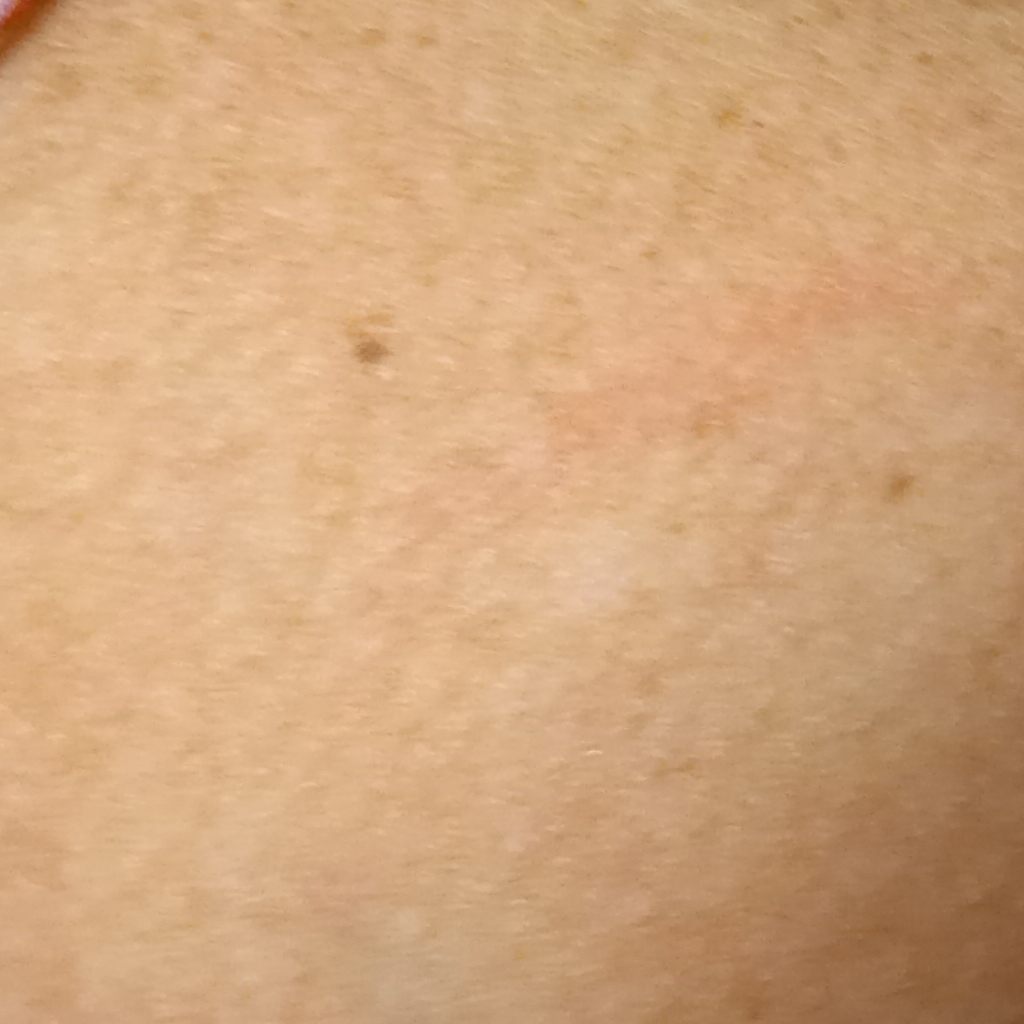The patient says their skin reddens with sun exposure.
By self-report, a personal history of skin cancer, no personal history of cancer, and no immunosuppression.
A female patient age 67.
Acquired for a research image collection, with no referral diagnosis.
The lesion involves an arm.
The lesion measures approximately 1.3 mm.
Dermatologist review favored a melanocytic nevus.